Fitzpatrick II · this image was taken at a distance:
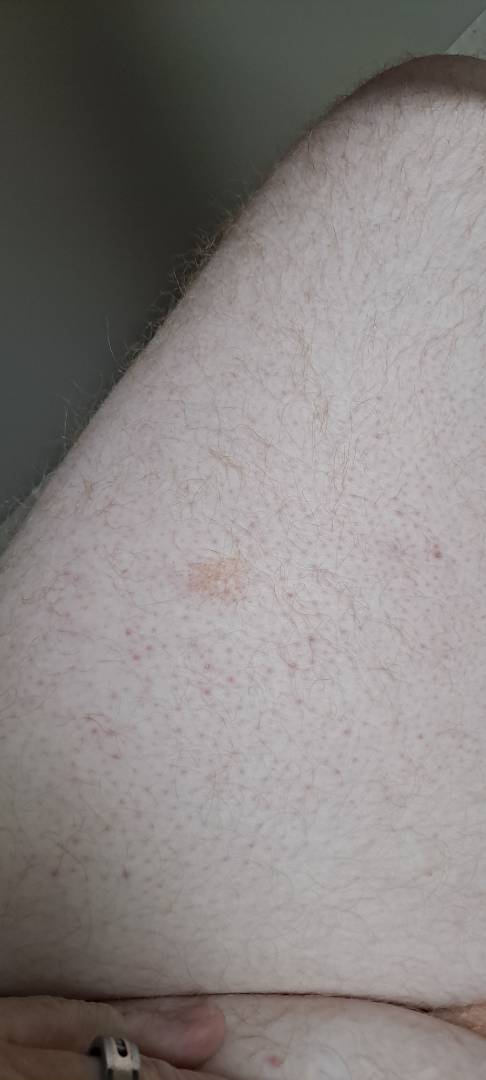Impression:
Diagnostic features were not clearly distinguishable in this photograph.